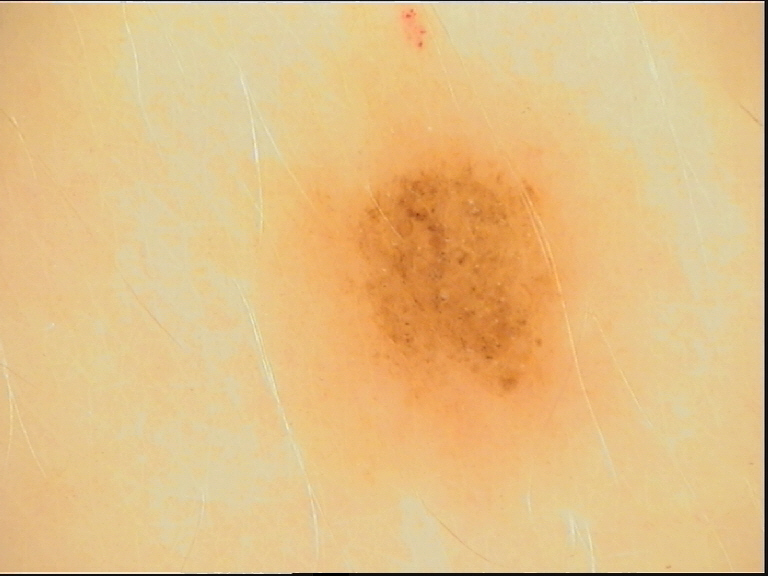Consistent with a dysplastic junctional nevus.